A clinical photograph showing a skin lesion in context — 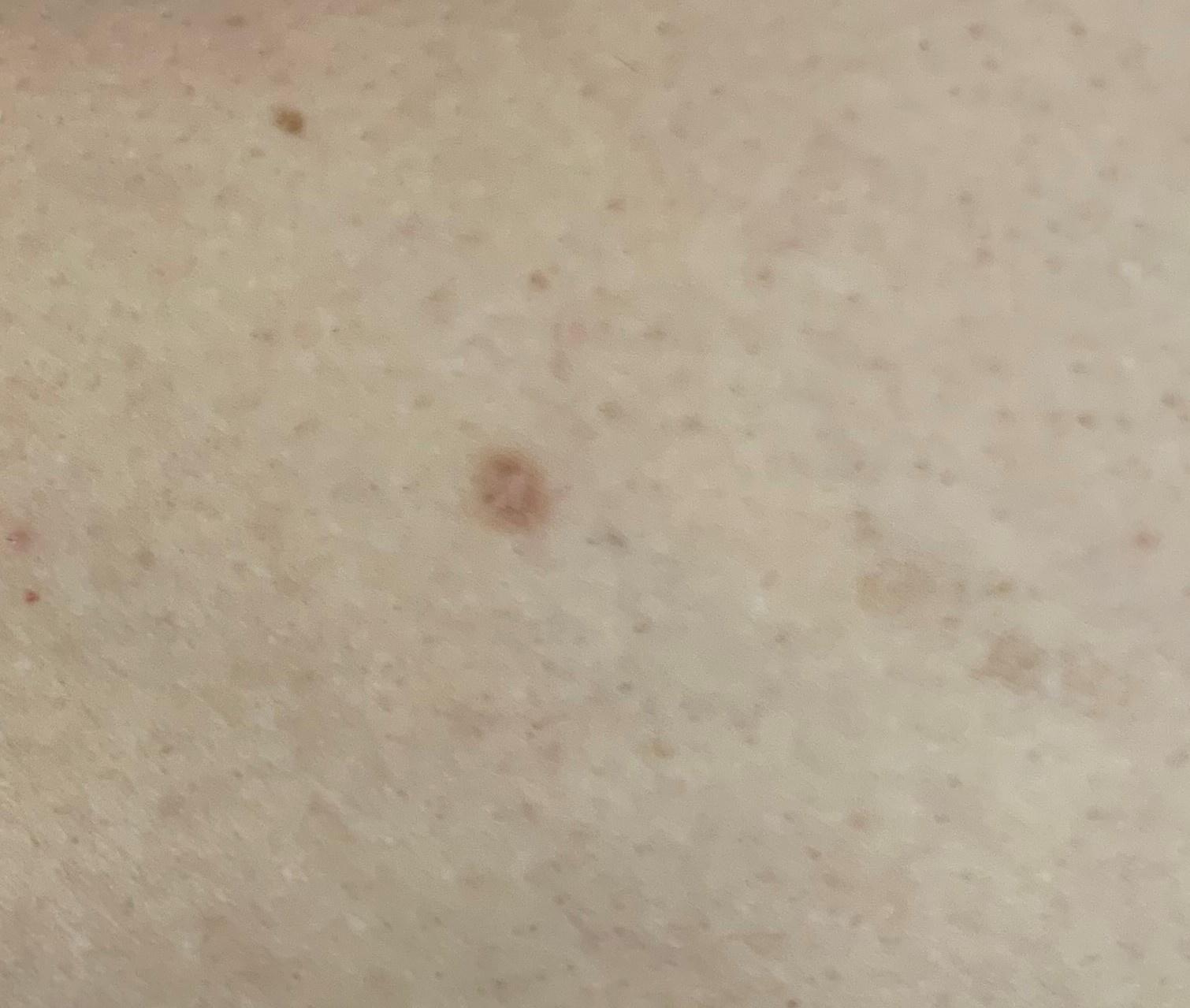Clinical context:
The lesion is on a lower extremity.
Conclusion:
The clinical assessment was a dermatofibroma.